A skin lesion imaged with a dermatoscope.
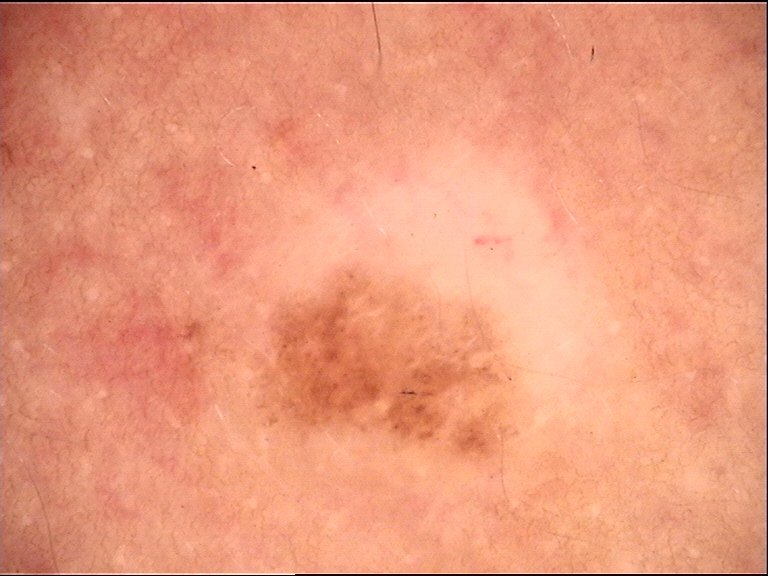| feature | finding |
|---|---|
| lesion type | banal |
| diagnostic label | compound nevus (expert consensus) |